This image was taken at an angle · human graders estimated MST 3 or 5.
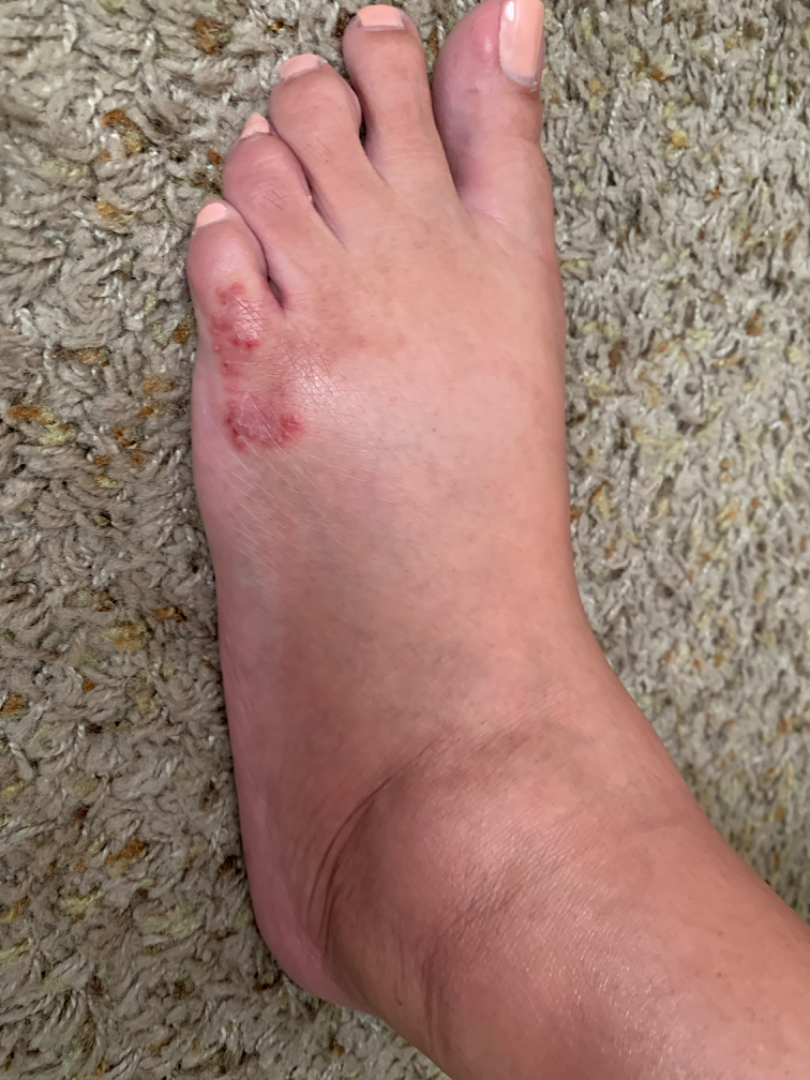differential diagnosis: Eczema and Allergic Contact Dermatitis were considered with similar weight.